A close-up photograph; the lesion involves the leg; the contributor is a female aged 60–69: 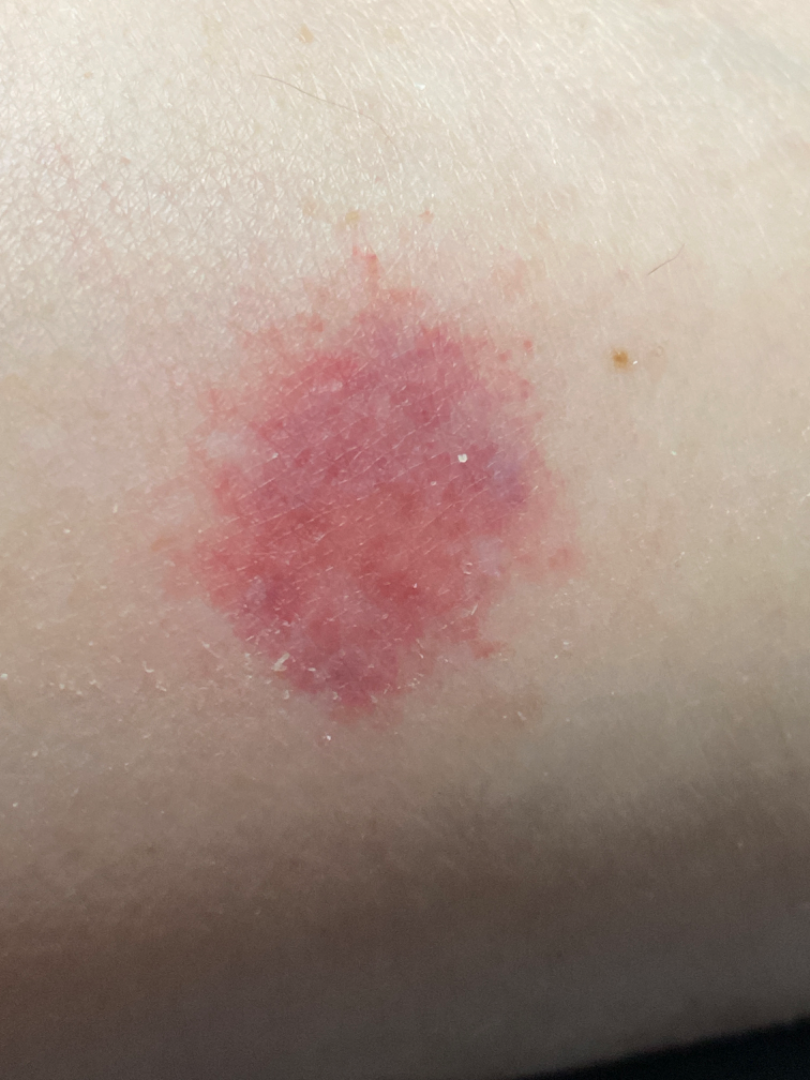* associated systemic symptoms: none reported
* self-categorized as: a rash
* lesion symptoms: itching and bothersome appearance
* skin tone: Fitzpatrick skin type I
* onset: less than one week
* texture: raised or bumpy
* differential diagnosis: Eczema and Allergic Contact Dermatitis were each considered, in no particular order; less likely is Purpura